The photograph is a close-up of the affected area; reported duration is about one day; no associated systemic symptoms reported; the contributor notes bothersome appearance, itching and darkening; the patient considered this a rash; the lesion involves the arm — 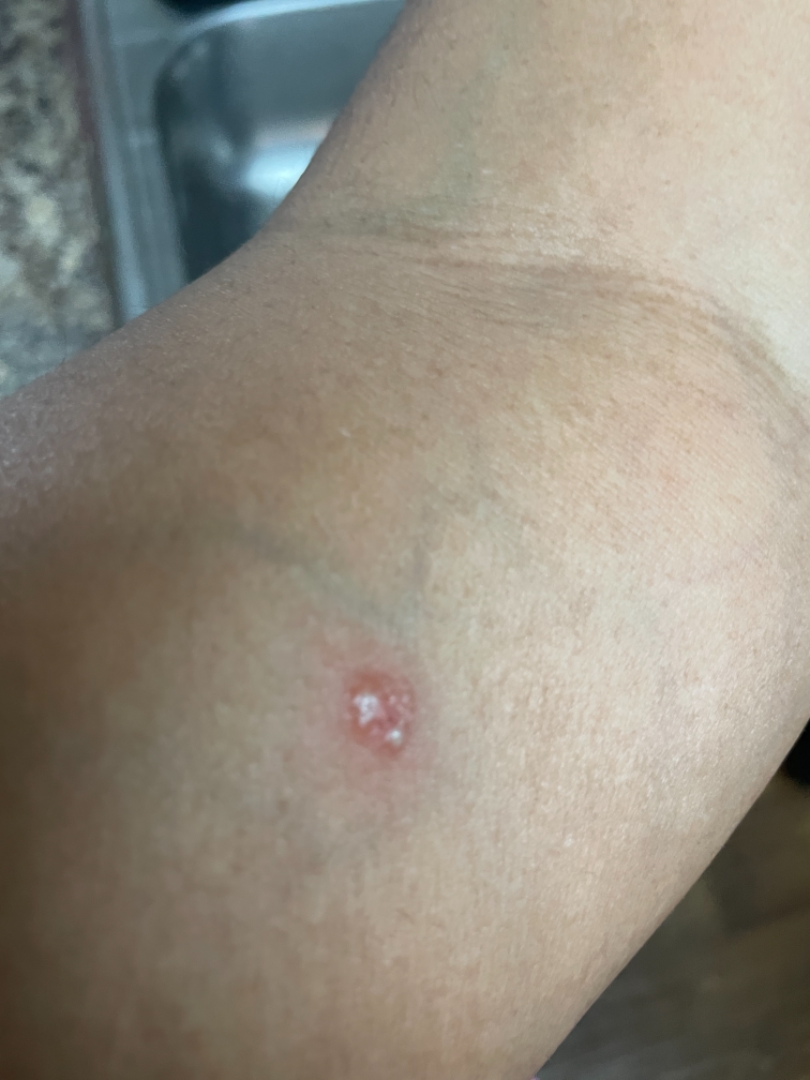impression=favoring Psoriasis; also raised was Eczema; also consider SCC/SCCIS